A dermatoscopic image of a skin lesion.
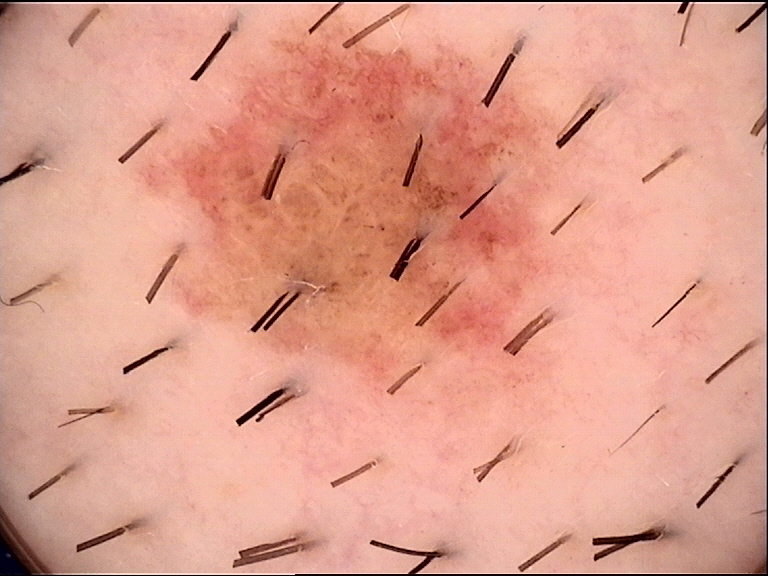{
  "diagnosis": {
    "name": "dysplastic compound nevus",
    "code": "cd",
    "malignancy": "benign",
    "super_class": "melanocytic",
    "confirmation": "expert consensus"
  }
}